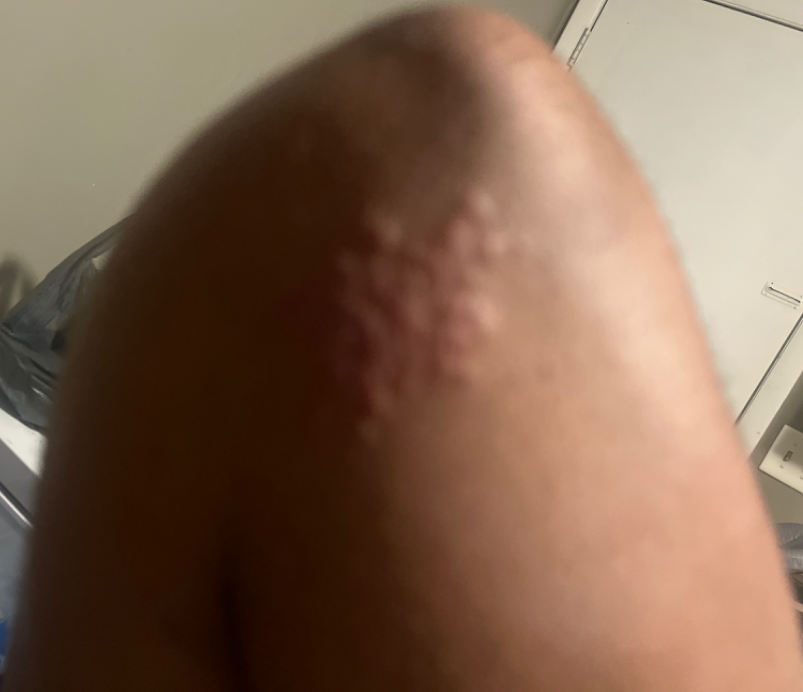Q: Image view?
A: at an angle
Q: What is the dermatologist's impression?
A: Herpes Zoster, Allergic Contact Dermatitis and Herpes Simplex were each considered, in no particular order